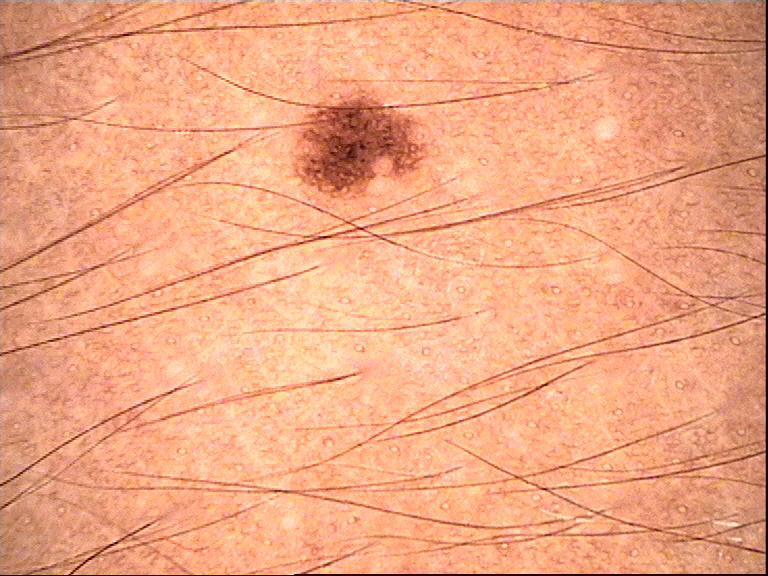Impression:
The diagnosis was a dysplastic junctional nevus.